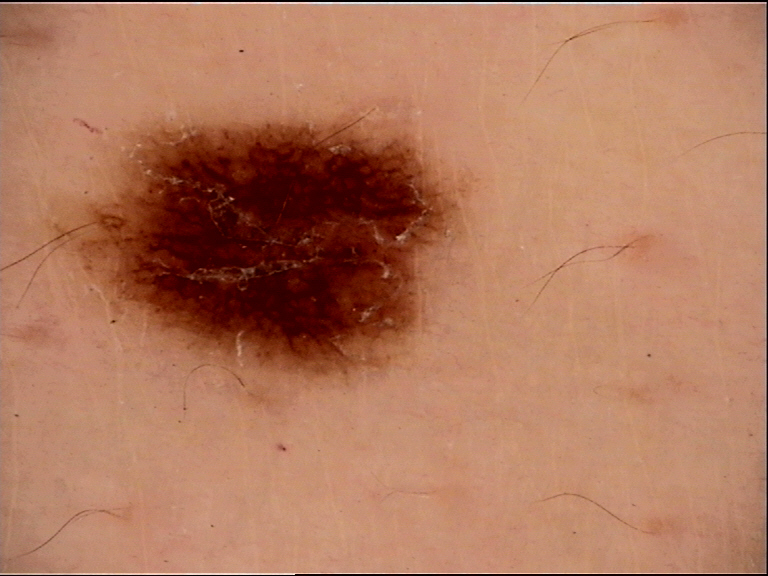label: dysplastic junctional nevus (expert consensus)